Dermoscopy of a skin lesion · a male subject, aged 48 to 52: 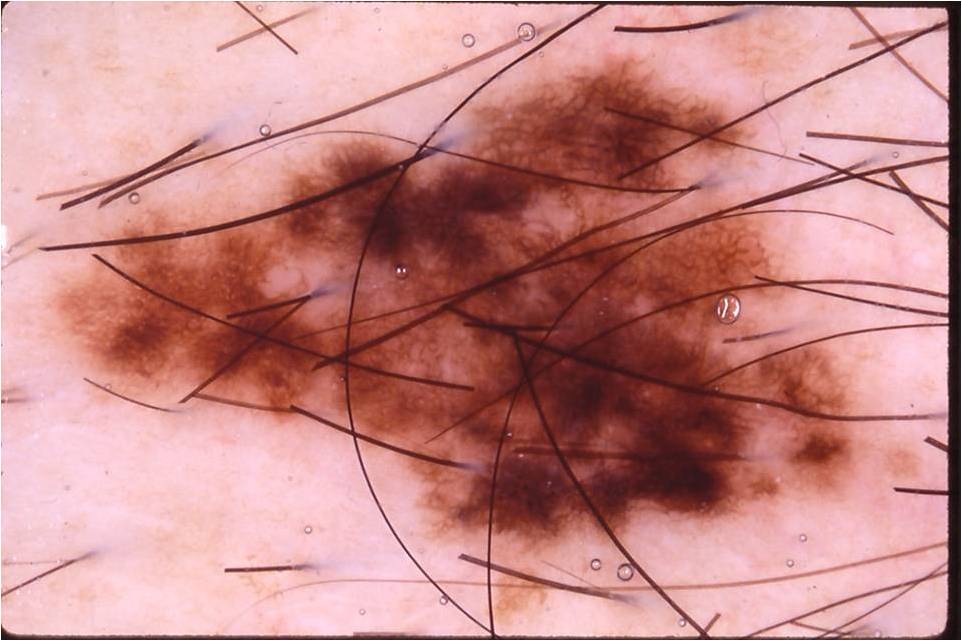Dermoscopically, the lesion shows pigment network. The lesion occupies roughly 43% of the field. In (x1, y1, x2, y2) order, the lesion's extent is bbox=[47, 51, 868, 562]. Consistent with a melanocytic nevus, a benign skin lesion.